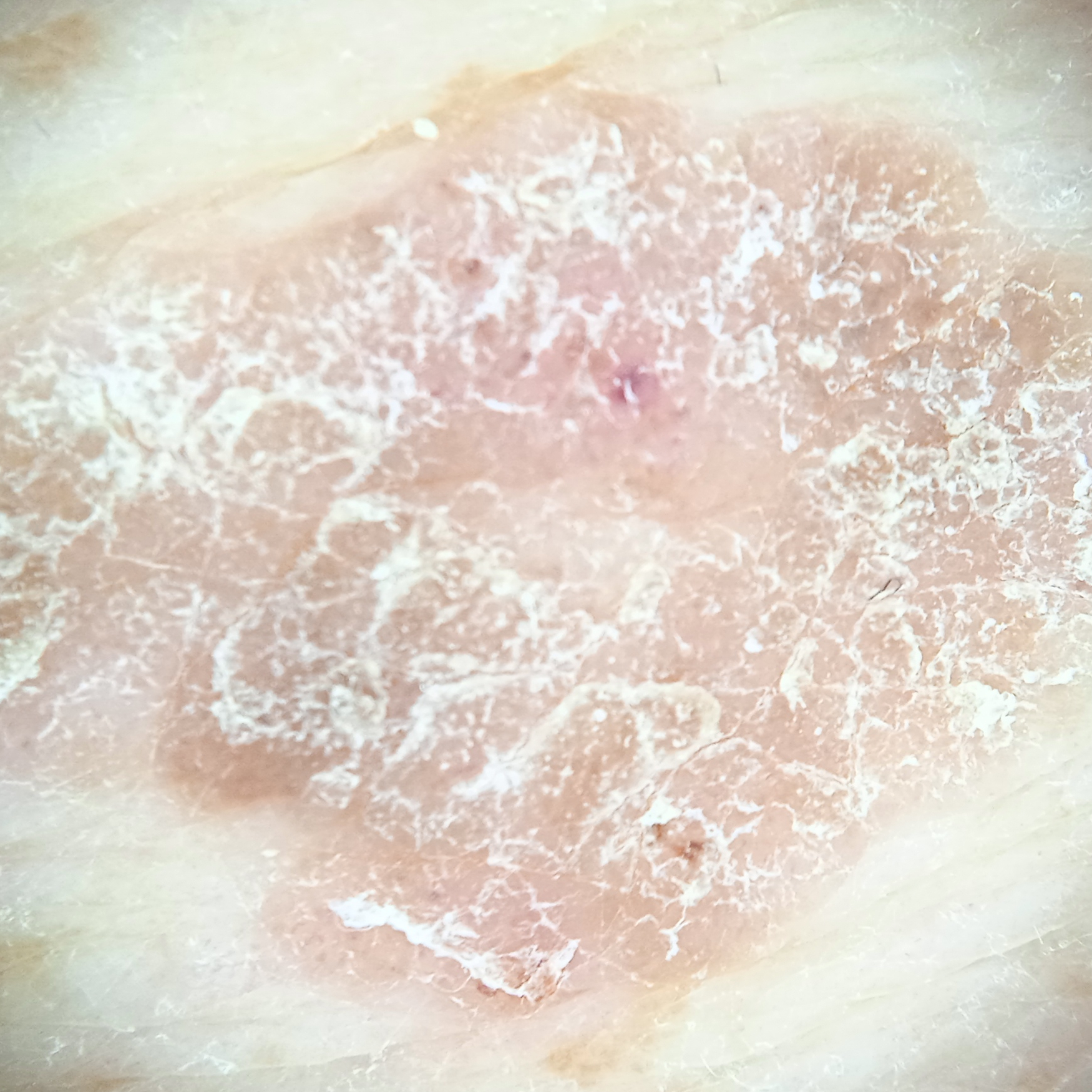Dermoscopy of a skin lesion. Imaged for a research study, with no referral diagnosis recorded. A male patient 72 years of age. The lesion is located on the back. Measuring roughly 16.5 mm. Dermatologist review favored a seborrheic keratosis.